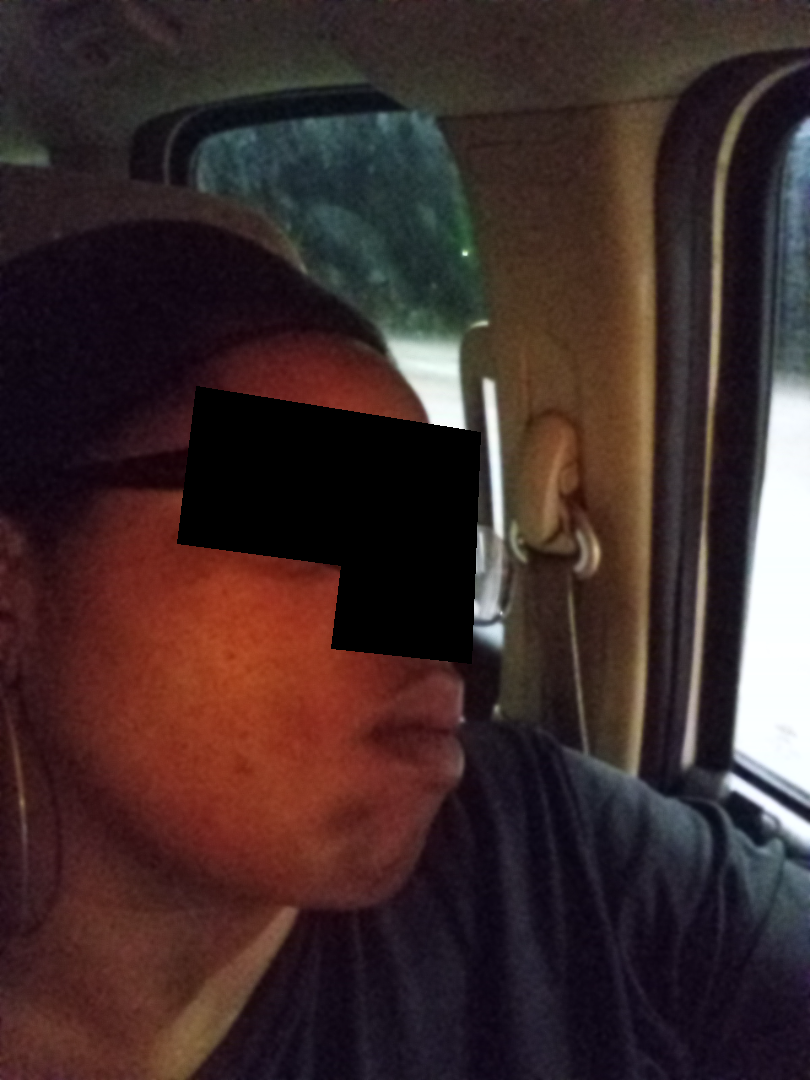assessment = could not be assessed
shot type = at a distance